Texture is reported as raised or bumpy. Reported lesion symptoms include itching and enlargement. The patient is a female aged 50–59. Skin tone: self-reported FST II. An image taken at an angle. The lesion involves the arm. Self-categorized by the patient as a rash. Present for one to four weeks. The patient reports associated fatigue — 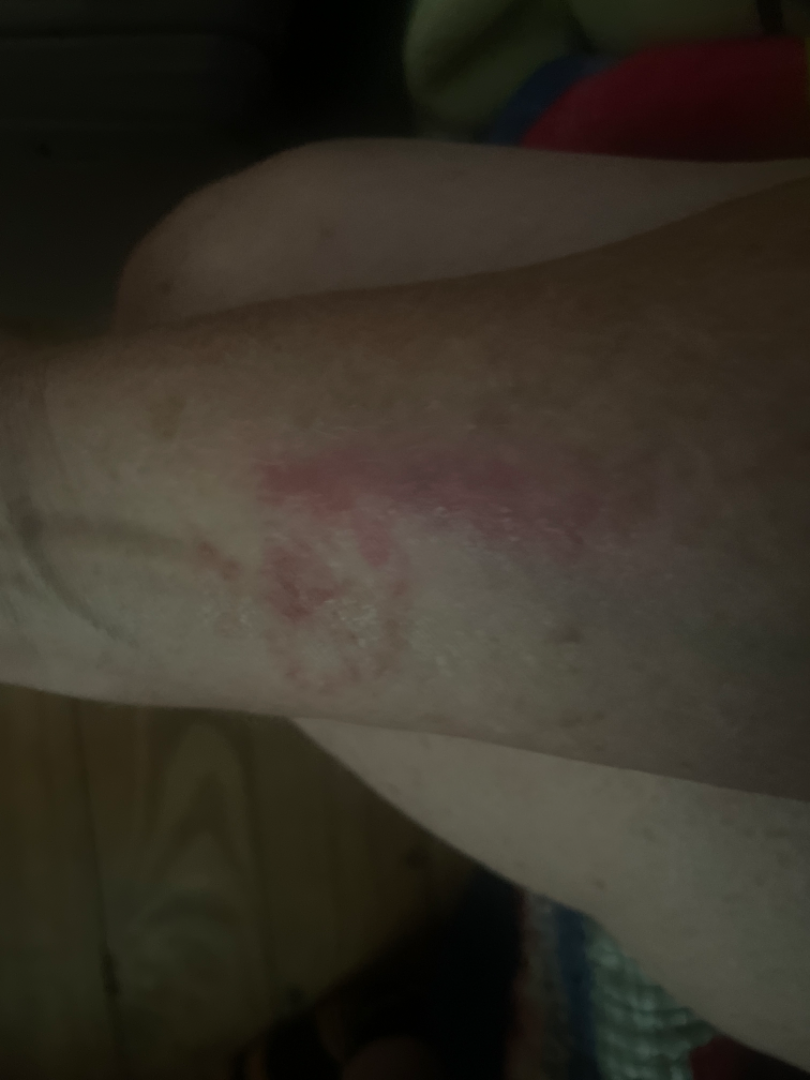Q: Could the case be diagnosed?
A: indeterminate